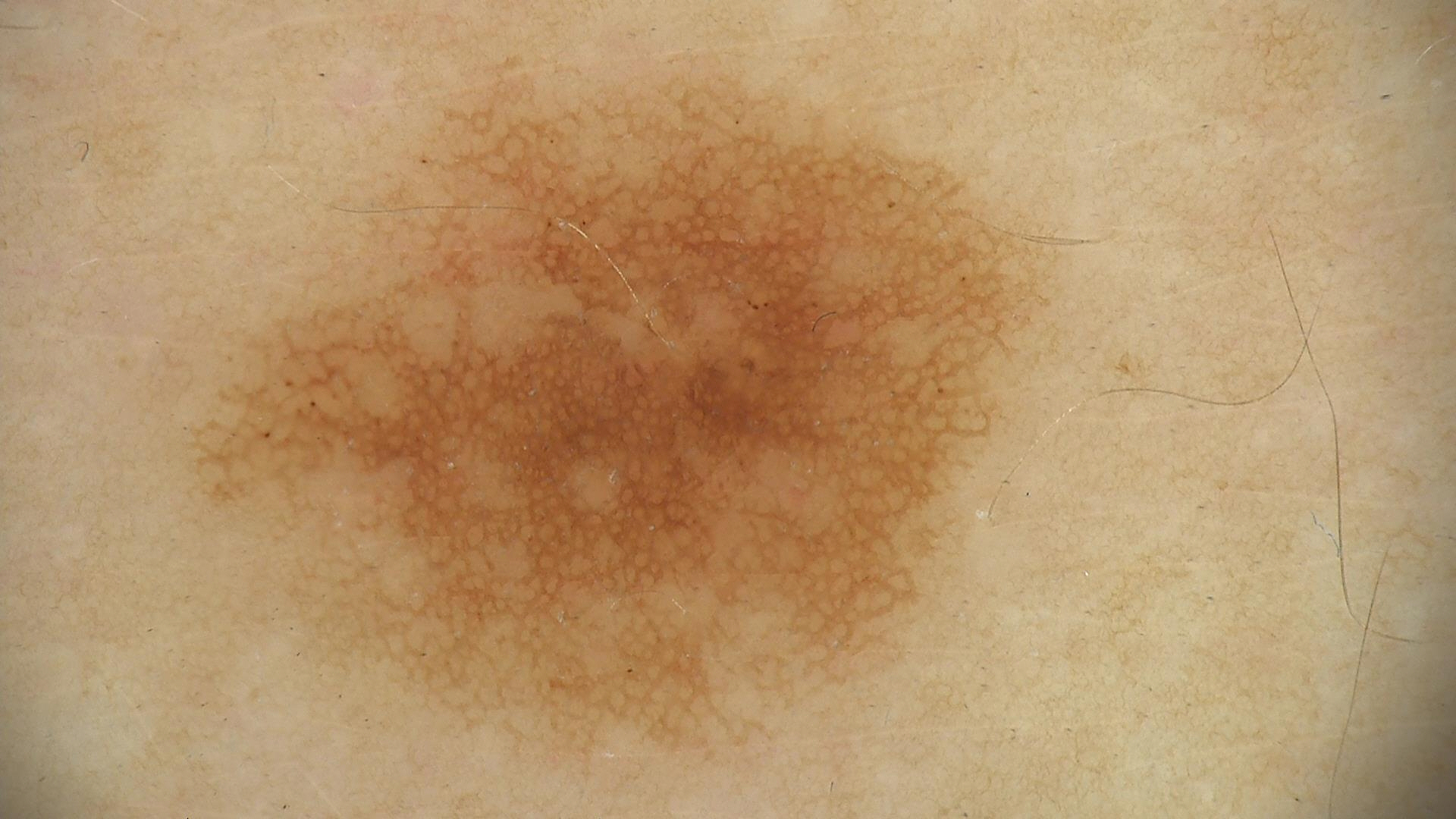image: dermoscopy
diagnosis:
  name: dysplastic junctional nevus
  code: jd
  malignancy: benign
  super_class: melanocytic
  confirmation: expert consensus